A dermatoscopic image of a skin lesion:
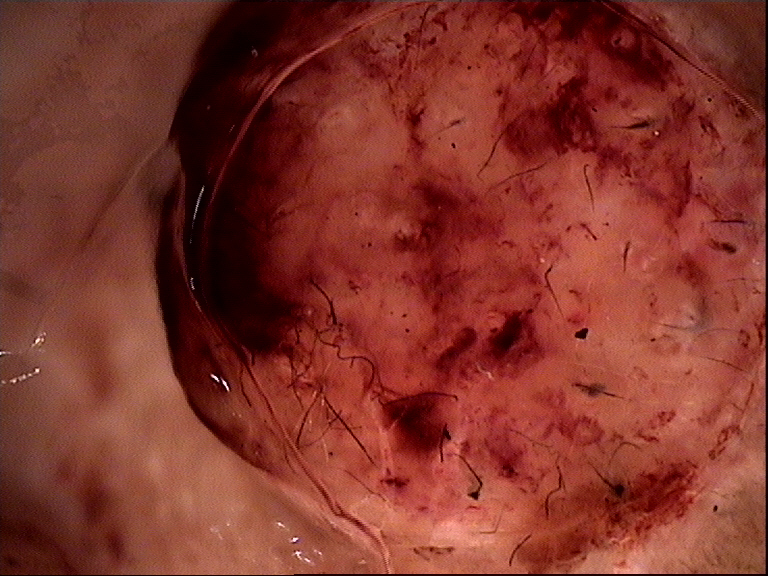Q: What is the diagnosis?
A: squamous cell carcinoma (biopsy-proven)